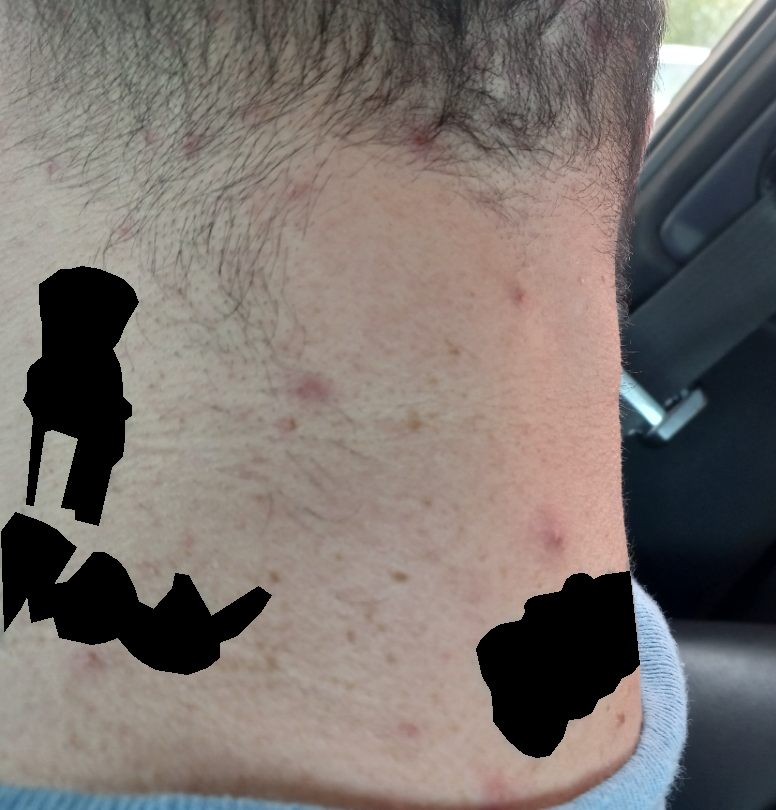Background:
The head or neck is involved. A close-up photograph. The subject is male.
Findings:
Single-reviewer assessment: most consistent with Acne; also raised was Folliculitis; a remote consideration is Acne keloidalis.